This is a close-up image. The lesion involves the arm: 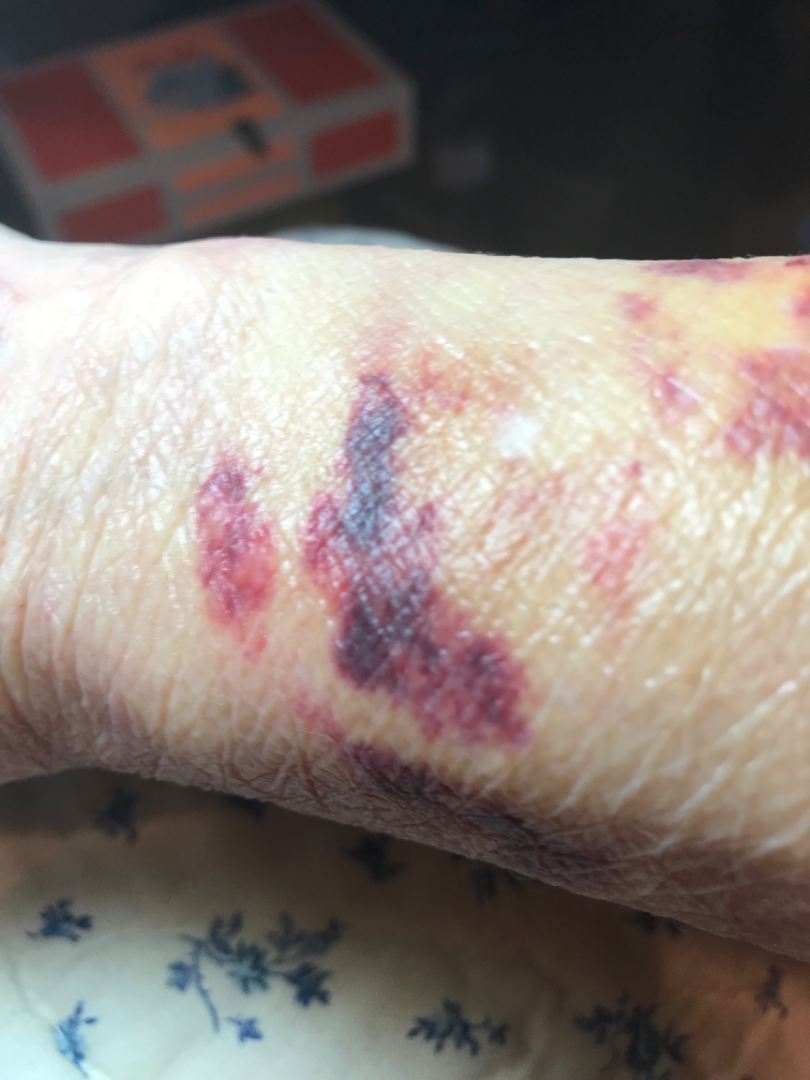Findings: On photographic review by a dermatologist: ecchymoses (leading).